A patient 37 years of age: 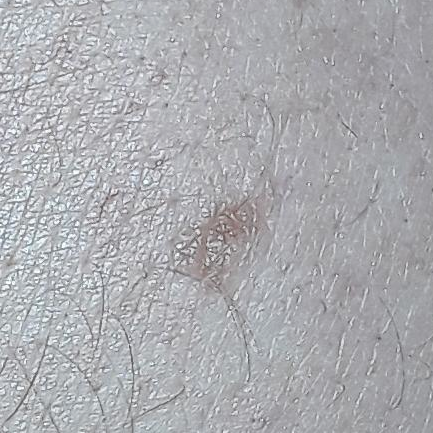| key | value |
|---|---|
| reported symptoms | growth / no pain |
| impression | nevus (clinical consensus) |